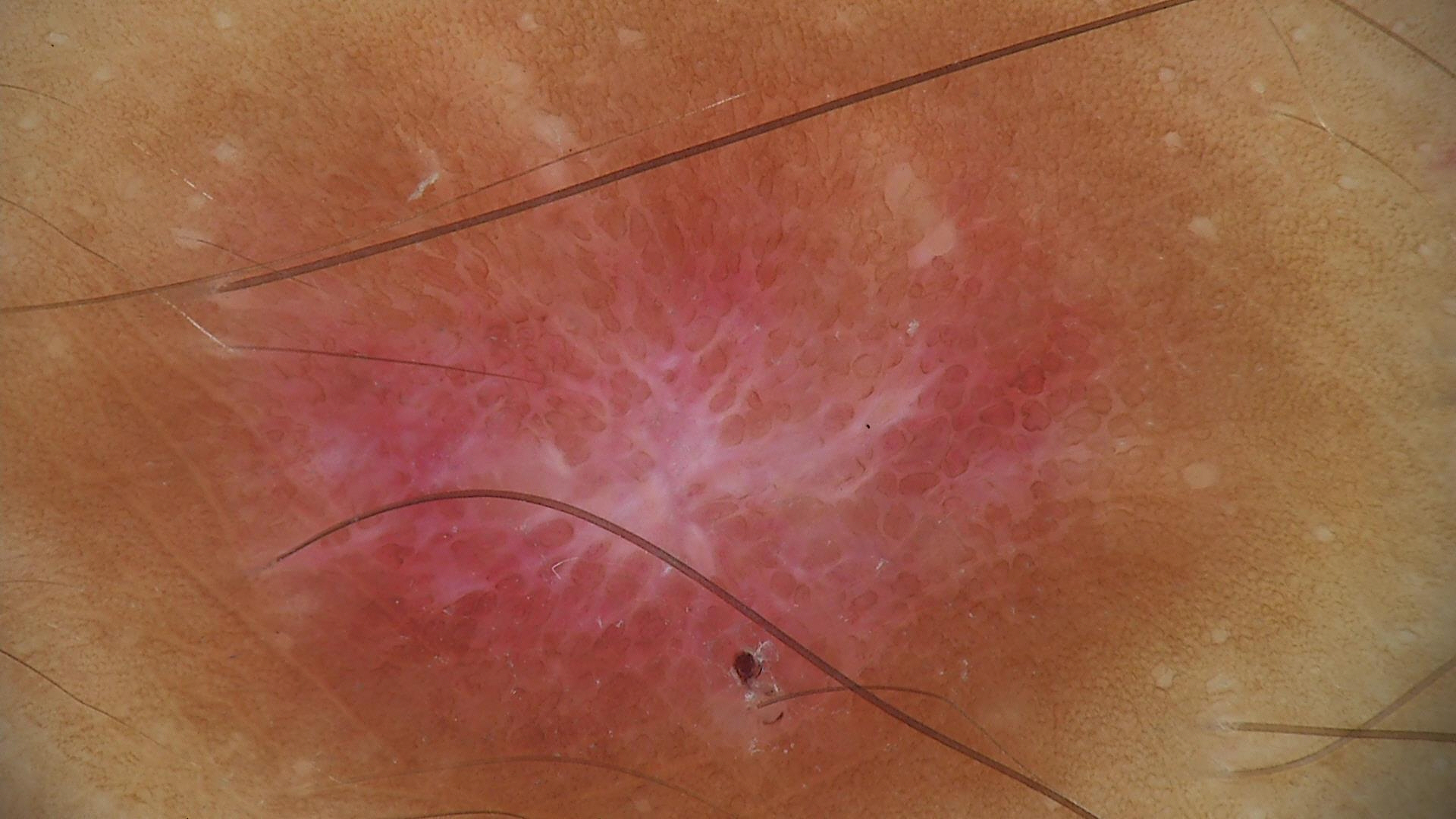A dermoscopic image of a skin lesion. Labeled as a fibro-histiocytic lesion — a dermatofibroma.